The contributor reports bothersome appearance · the photograph was taken at an angle · no associated systemic symptoms reported · self-categorized by the patient as skin that appeared healthy to them · reported duration is less than one week · the lesion is described as rough or flaky and raised or bumpy · the subject is 18–29, female:
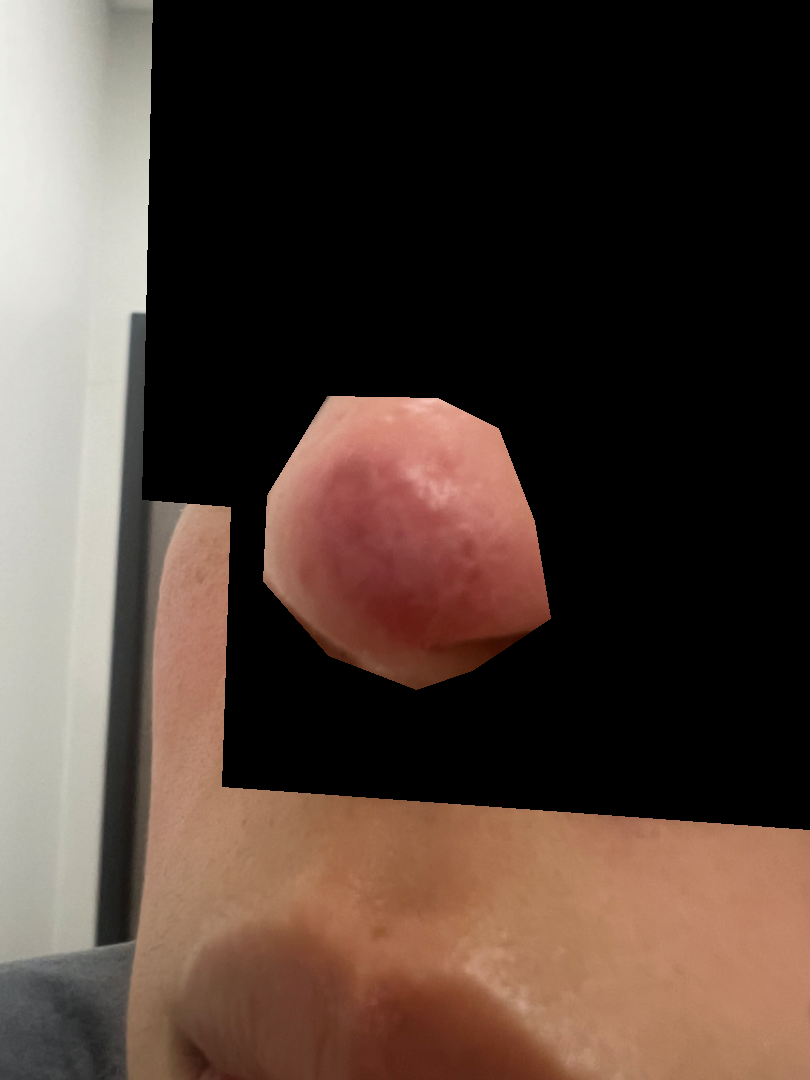The image was not sufficient for the reviewer to characterize the skin condition.